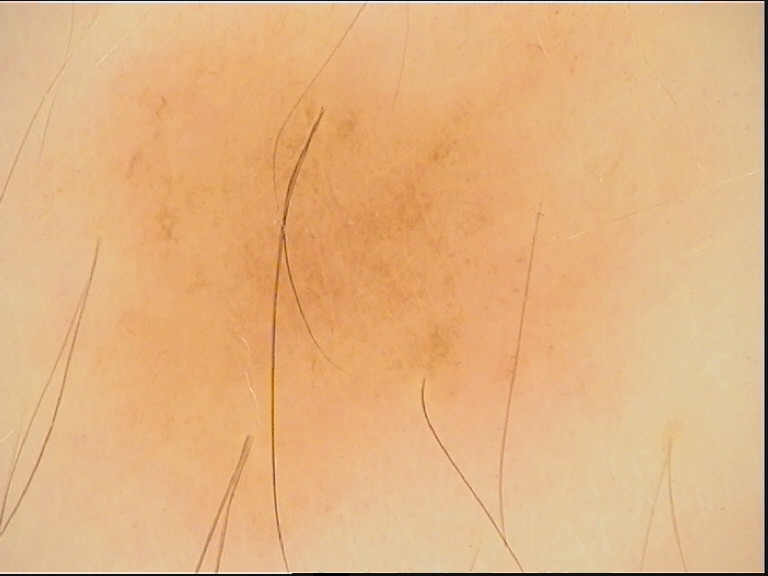A dermoscopic image of a skin lesion. Consistent with a banal lesion — a junctional nevus.